Female subject, age 40–49. Close-up view. Located on the leg.
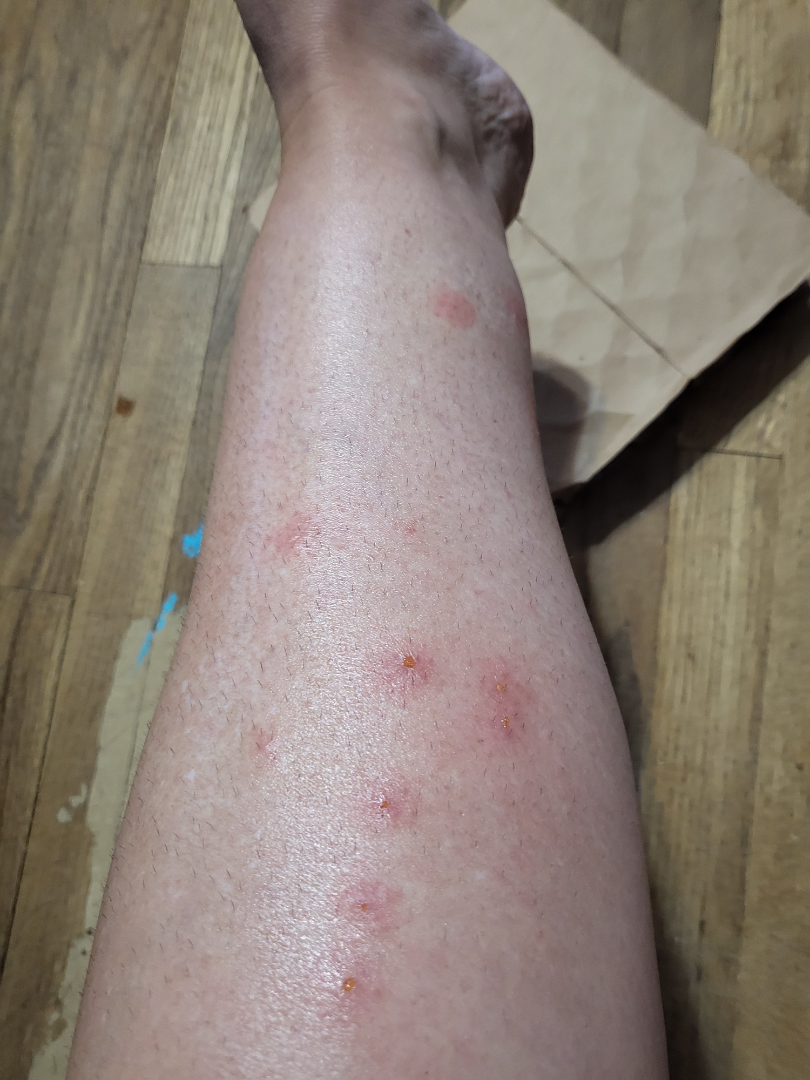| key | value |
|---|---|
| lesion texture | raised or bumpy, fluid-filled and rough or flaky |
| lesion symptoms | itching |
| onset | about one day |
| skin tone | Fitzpatrick skin type III |
| patient's own categorization | a rash |
| diagnostic considerations | most consistent with Insect Bite; also raised was Localized skin infection; an alternative is Allergic Contact Dermatitis |